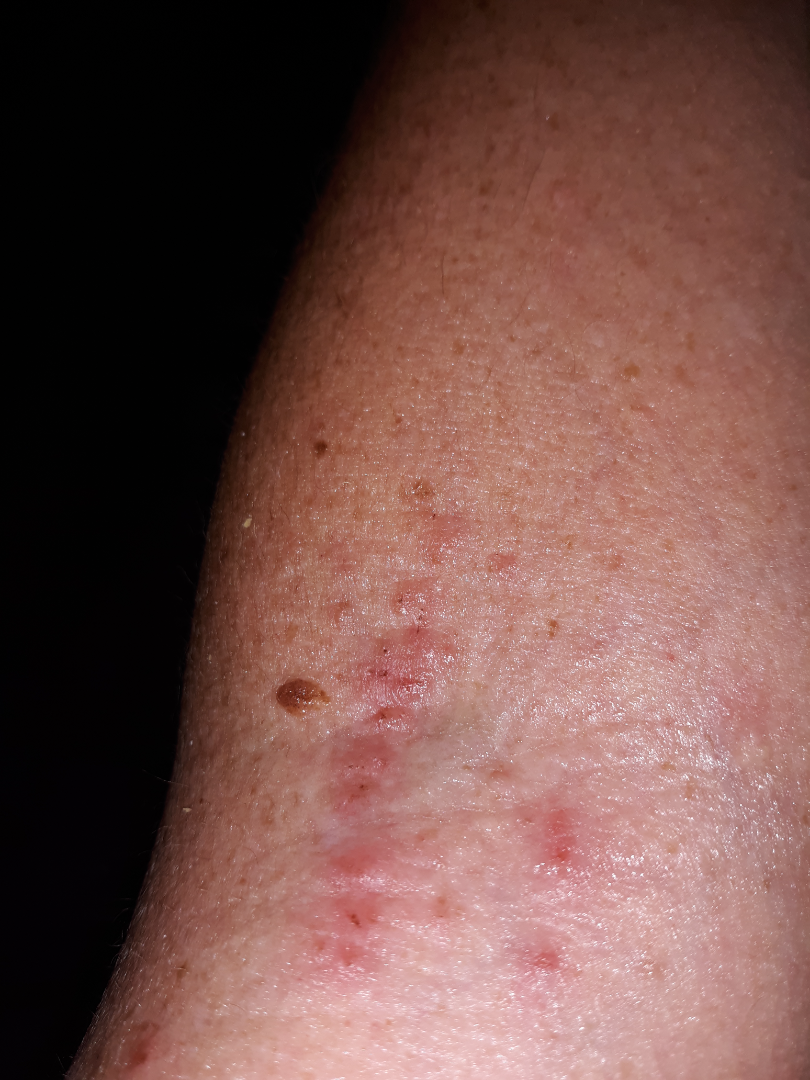History: The photo was captured at an angle.